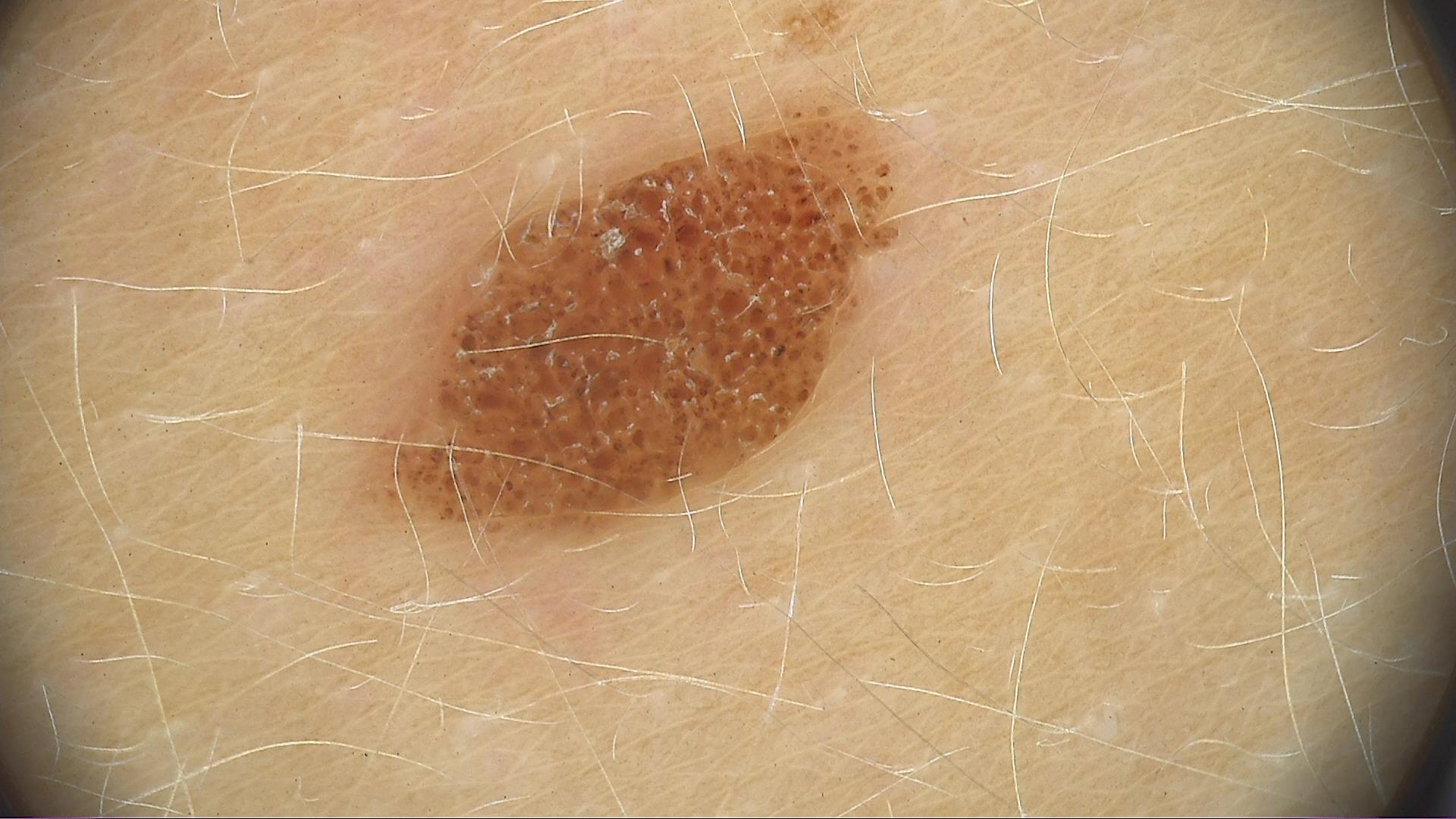image=dermoscopy
class=compound nevus (expert consensus)